A male subject in their mid- to late 60s · the patient was assessed as FST II · a dermoscopic image of a skin lesion — 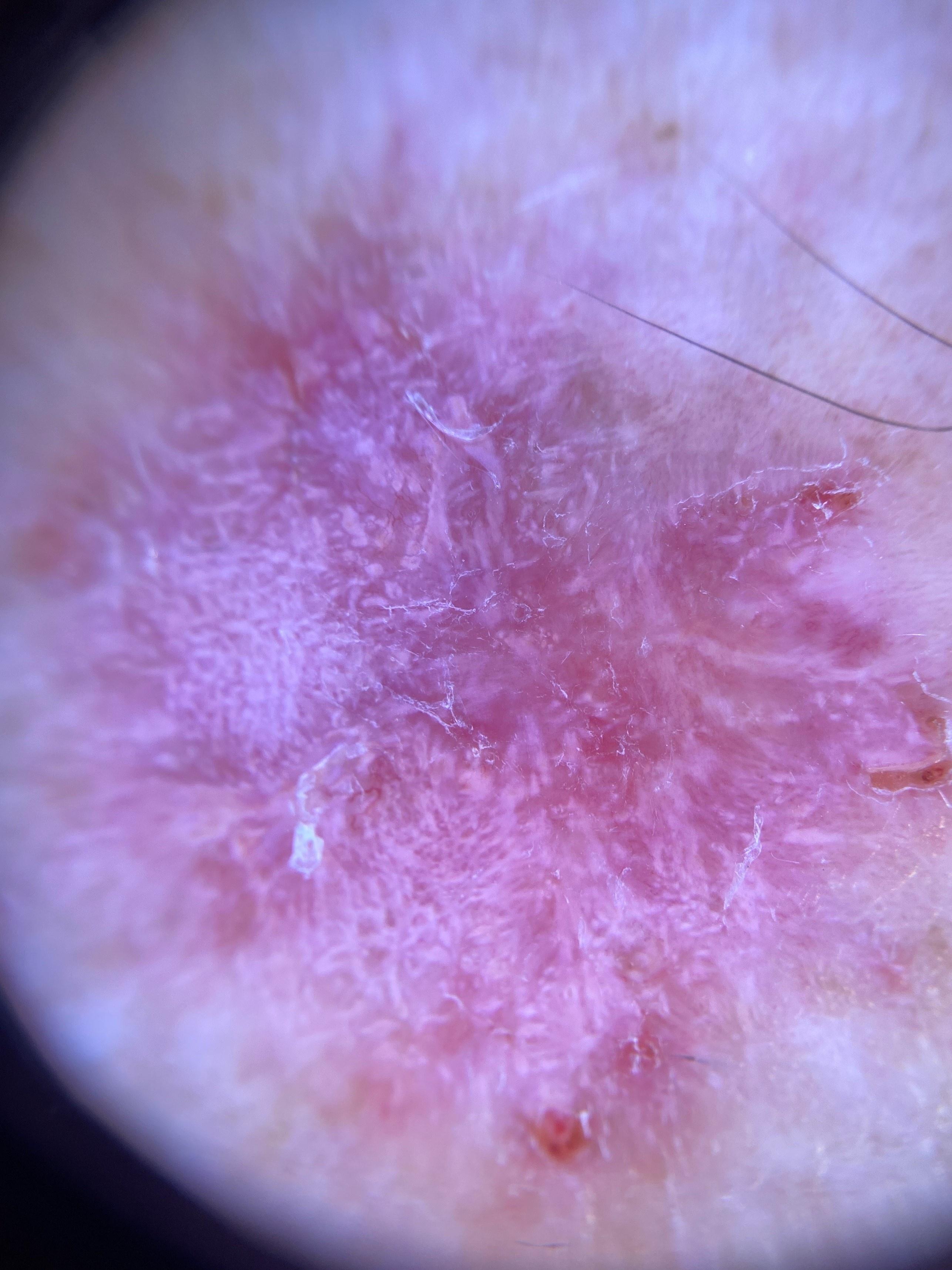The lesion was found on a lower extremity. Biopsy-confirmed as a basal cell carcinoma.